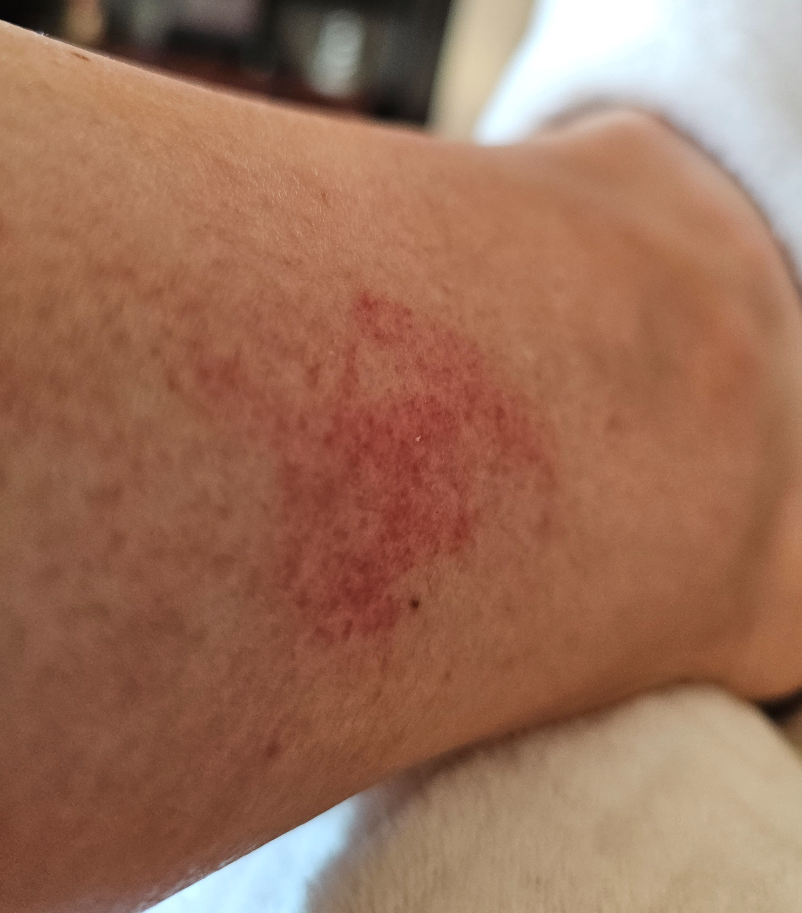Assessment:
The case was indeterminate on photographic review.
Clinical context:
No constitutional symptoms were reported. The affected area is the leg. Reported duration is about one day. Texture is reported as flat. The photo was captured at an angle. No relevant lesion symptoms reported.